A dermatoscopic image of a skin lesion; a male subject, in their mid- to late 70s.
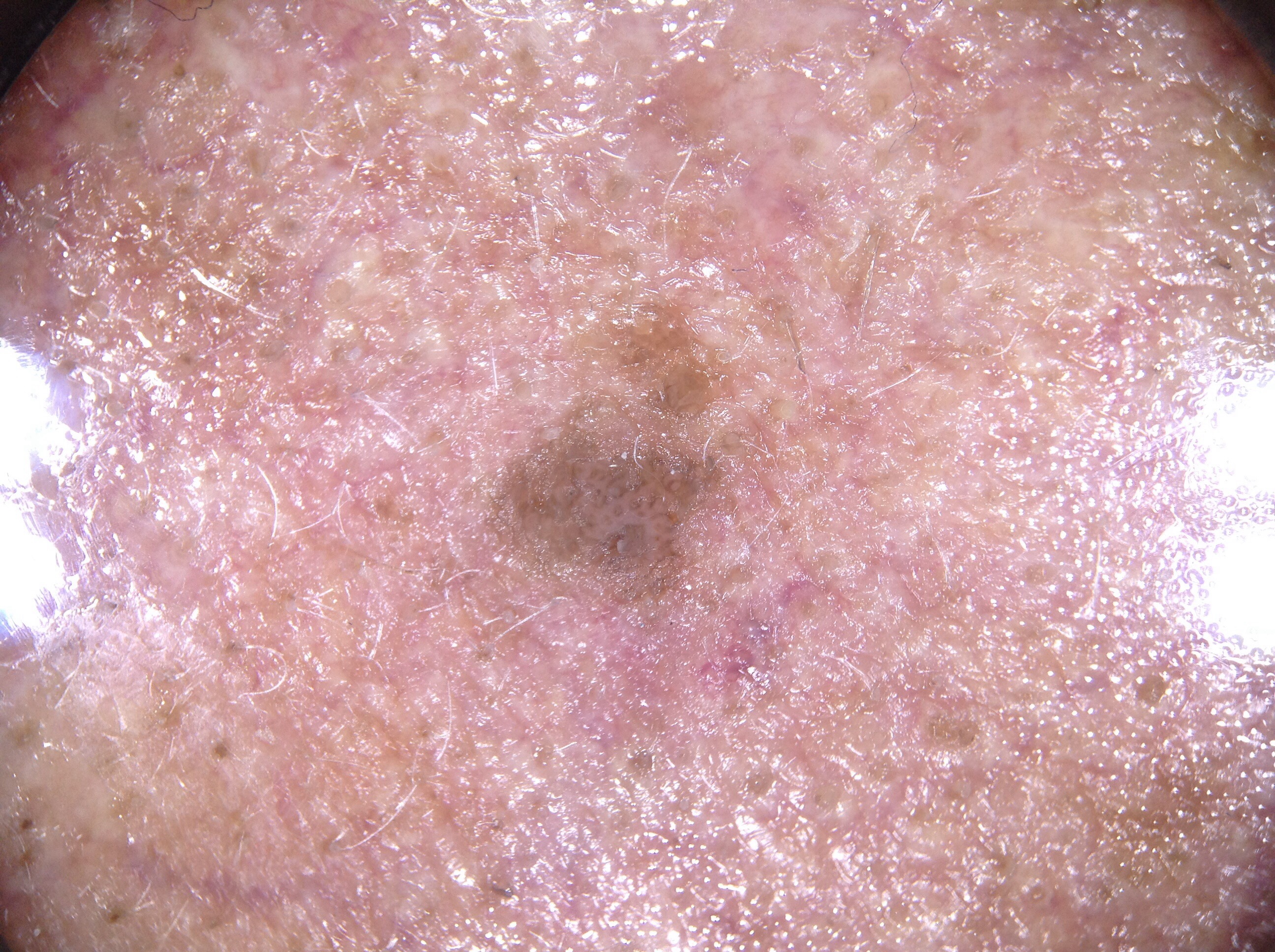Summary:
On dermoscopy, the lesion shows no milia-like cysts, streaks, negative network, or pigment network. A small lesion within a wider field of skin. As (left, top, right, bottom), the lesion is bounded by <bbox>482, 303, 766, 636</bbox>.
Impression:
Clinically diagnosed as a seborrheic keratosis, a benign skin lesion.